A dermatoscopic image of a skin lesion.
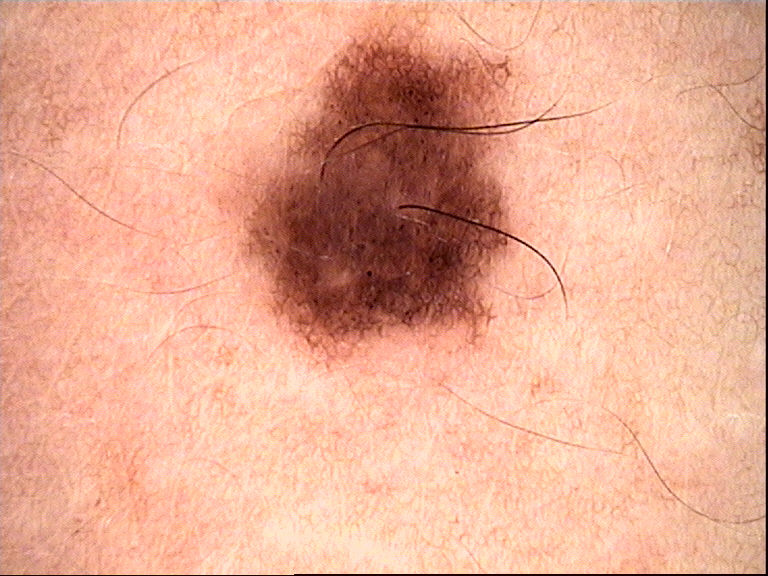label: dysplastic compound nevus (expert consensus).